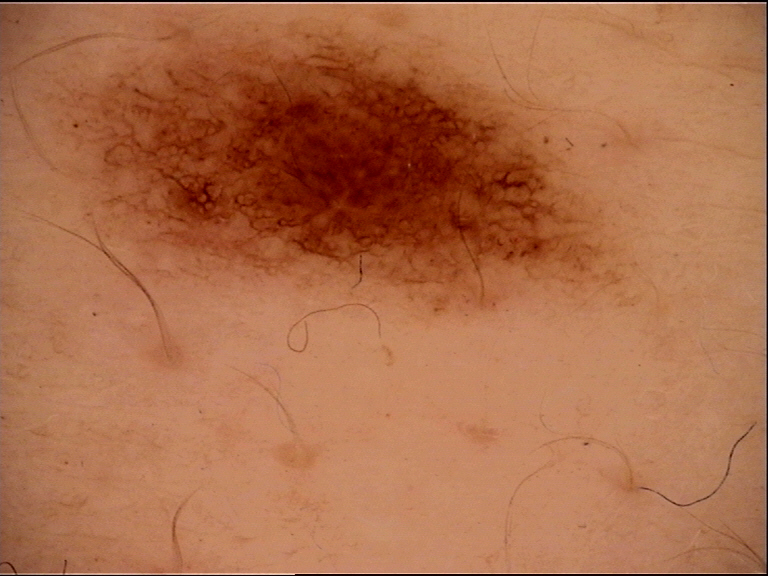The diagnostic label was a dysplastic junctional nevus.